A dermoscopic image of a skin lesion.
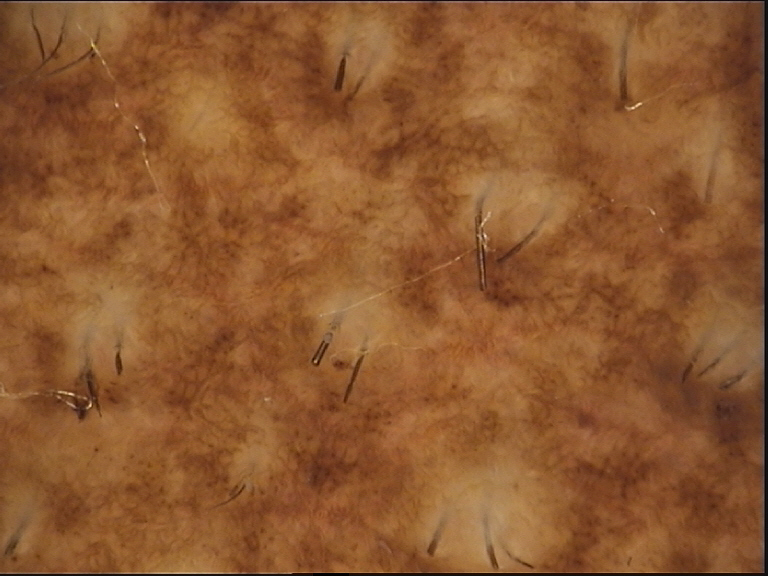The architecture is that of a banal lesion.
The diagnostic label was a congenital compound nevus.